A contact-polarized dermoscopy image of a skin lesion · a female subject aged 73 to 77:
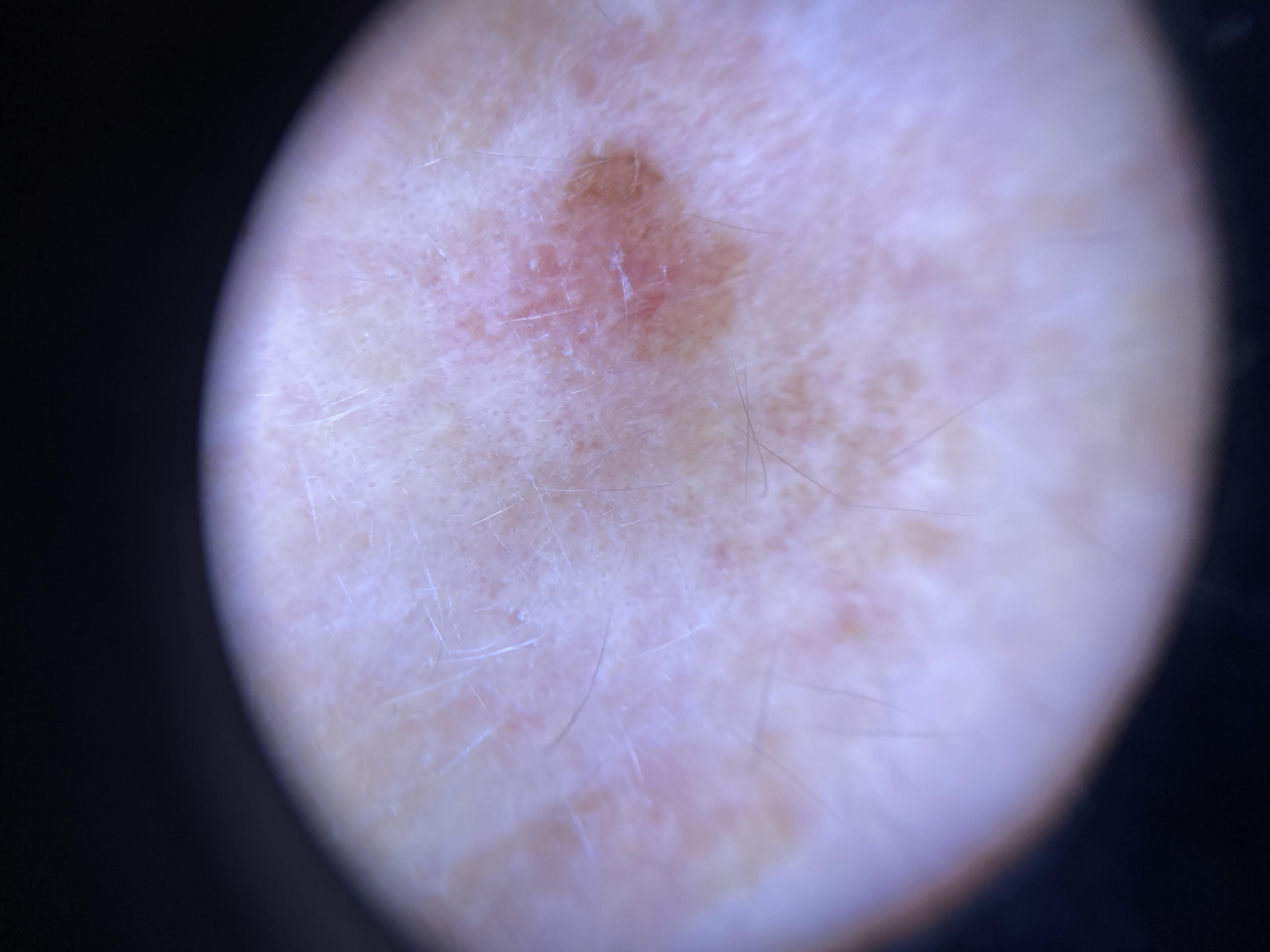– site · the head or neck
– diagnostic label · Melanoma (biopsy-proven)